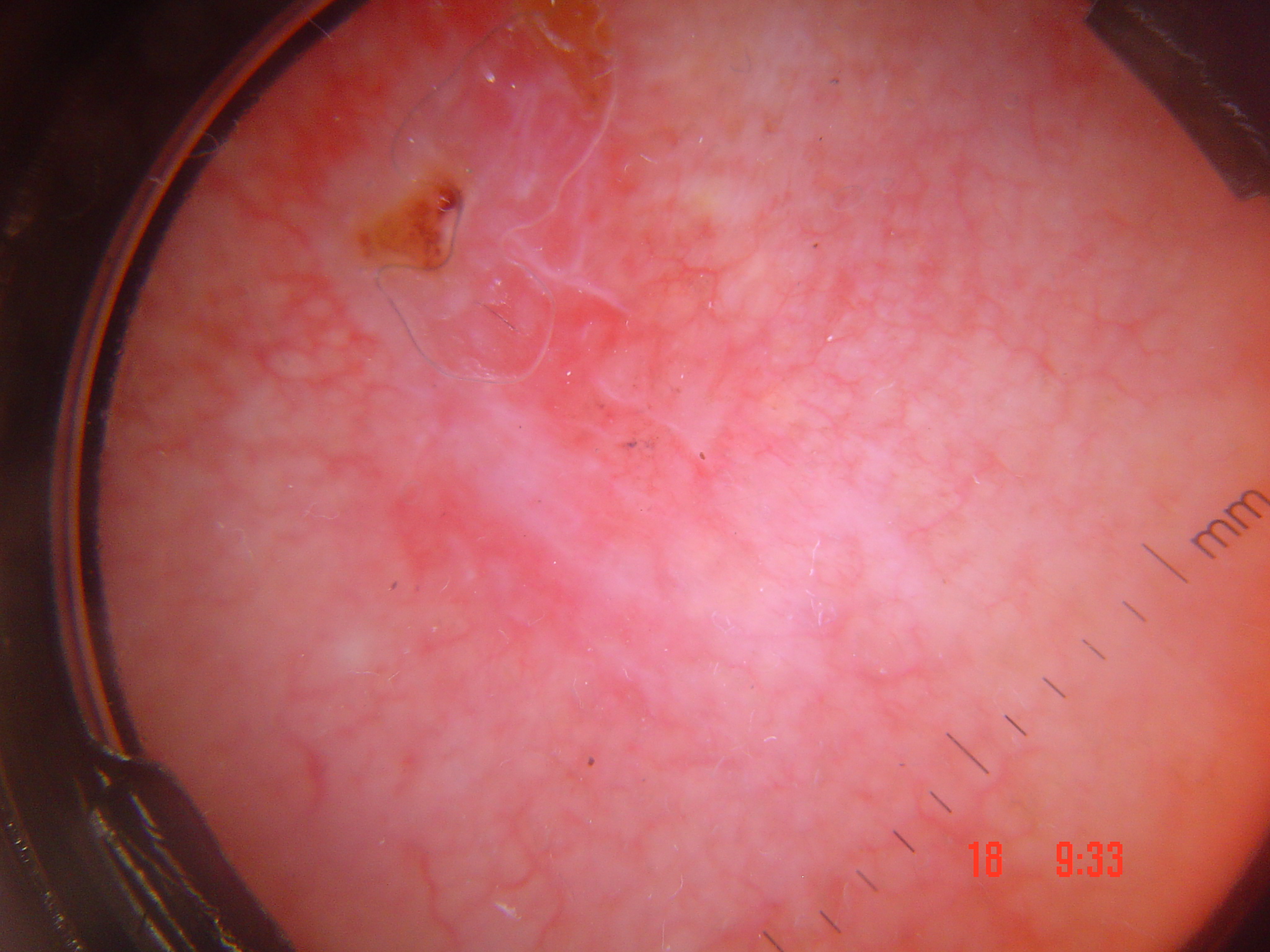imaging = dermatoscopy, category = keratinocytic, label = basal cell carcinoma (biopsy-proven).